A dermoscopy image of a single skin lesion.
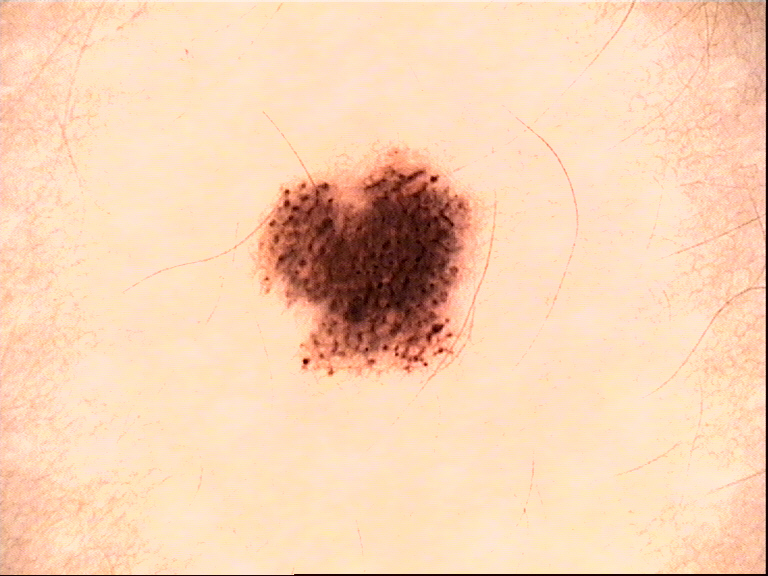This is a banal lesion.
Diagnosed as a compound nevus.